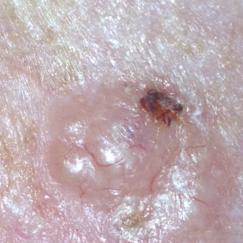skin phototype = I | image = clinical photograph | exposure history = prior skin cancer (patient or family), pesticide exposure, no alcohol use | site = the face | patient-reported symptoms = bleeding, itching, elevation, growth | pathology = basal cell carcinoma (biopsy-proven).